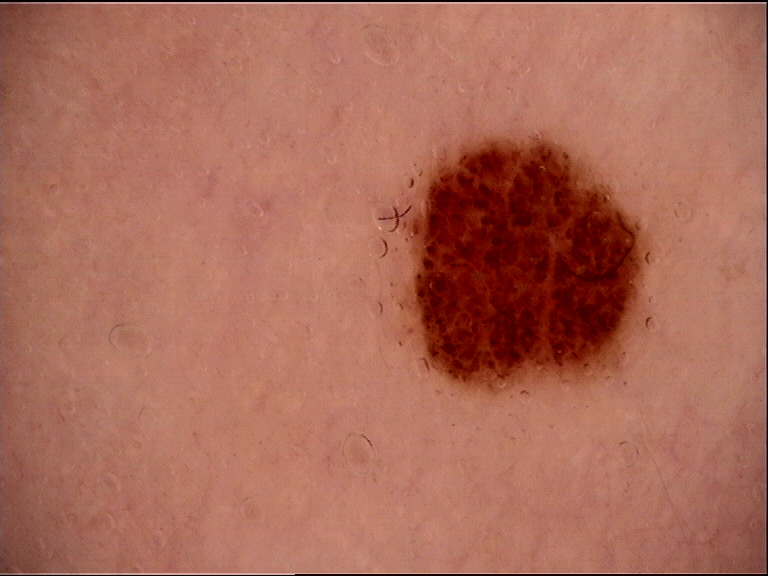Findings:
- modality · dermatoscopy
- lesion type · banal
- diagnostic label · compound nevus (expert consensus)